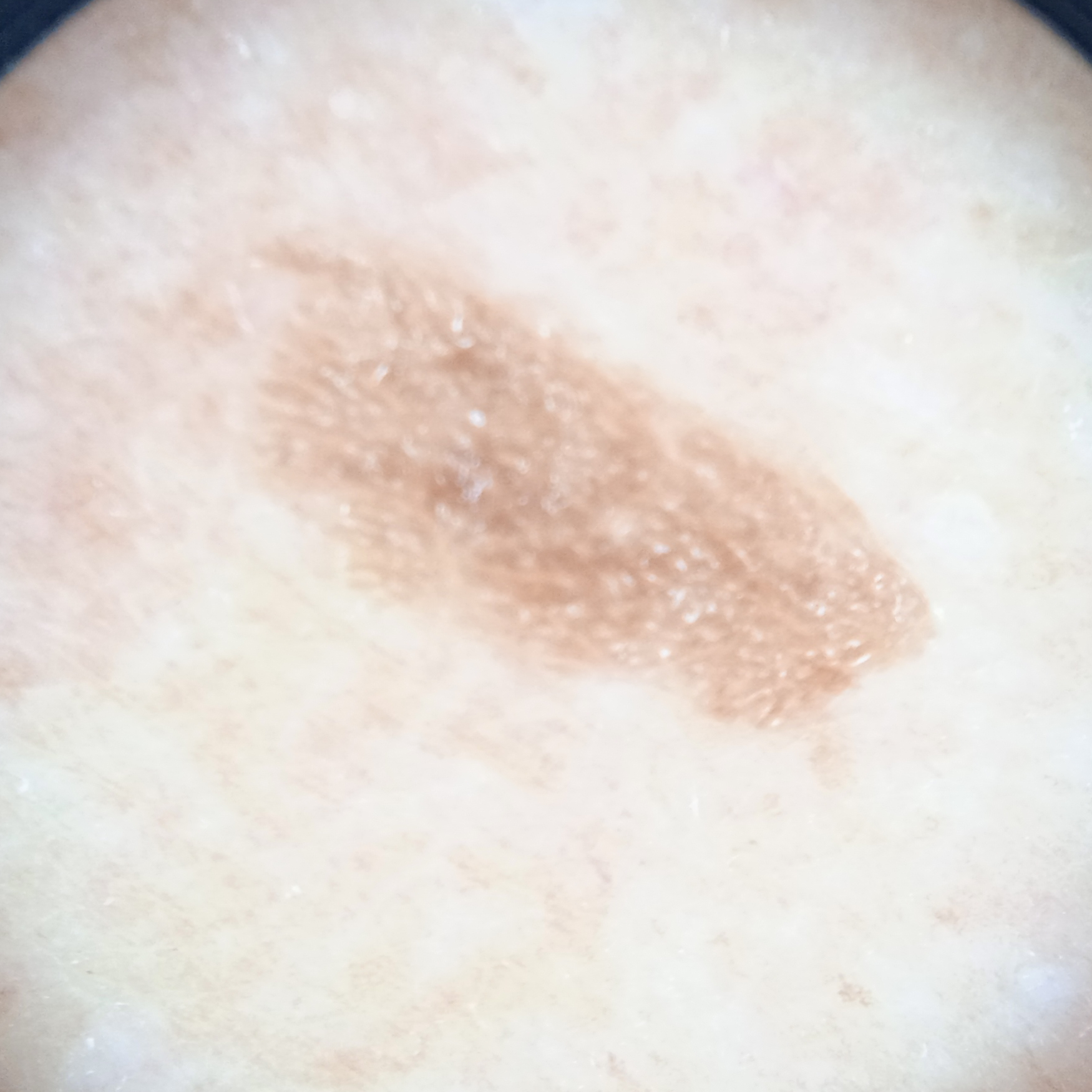Q: Why was this imaged?
A: research study (no referral diagnosis)
Q: What kind of image is this?
A: dermoscopy
Q: Patient demographics?
A: female, 75 years old
Q: What is the anatomic site?
A: the back
Q: How large is the lesion?
A: 8.4 mm
Q: What was the diagnosis?
A: seborrheic keratosis (dermatologist consensus)